A dermoscopy image of a single skin lesion:
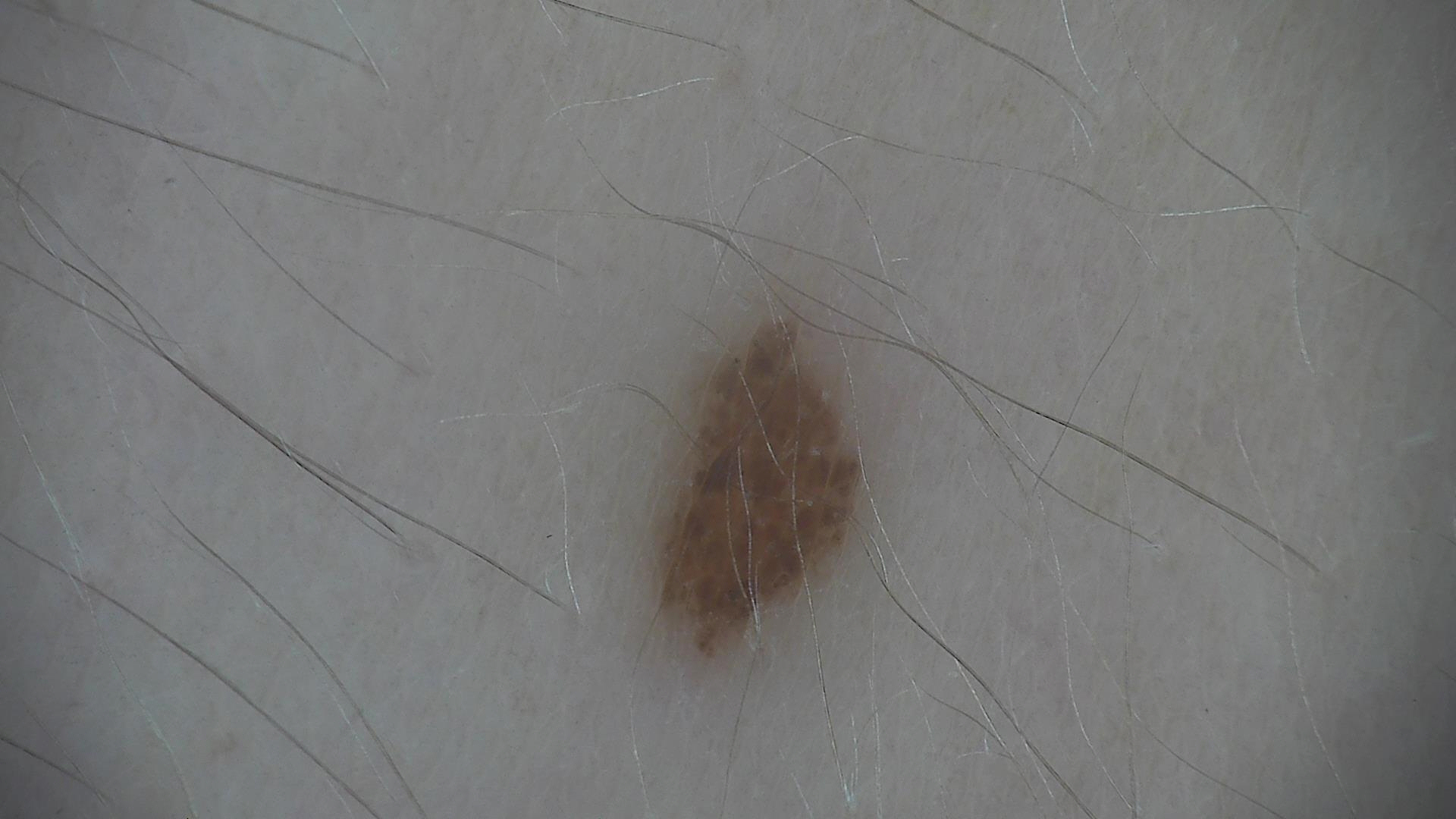Labeled as a benign lesion — a dysplastic junctional nevus.